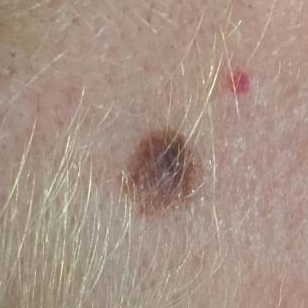patient: in their 70s
image type: clinical photograph
location: the face
reported symptoms: growth, elevation / no itching, no pain
assessment: seborrheic keratosis (clinical consensus)